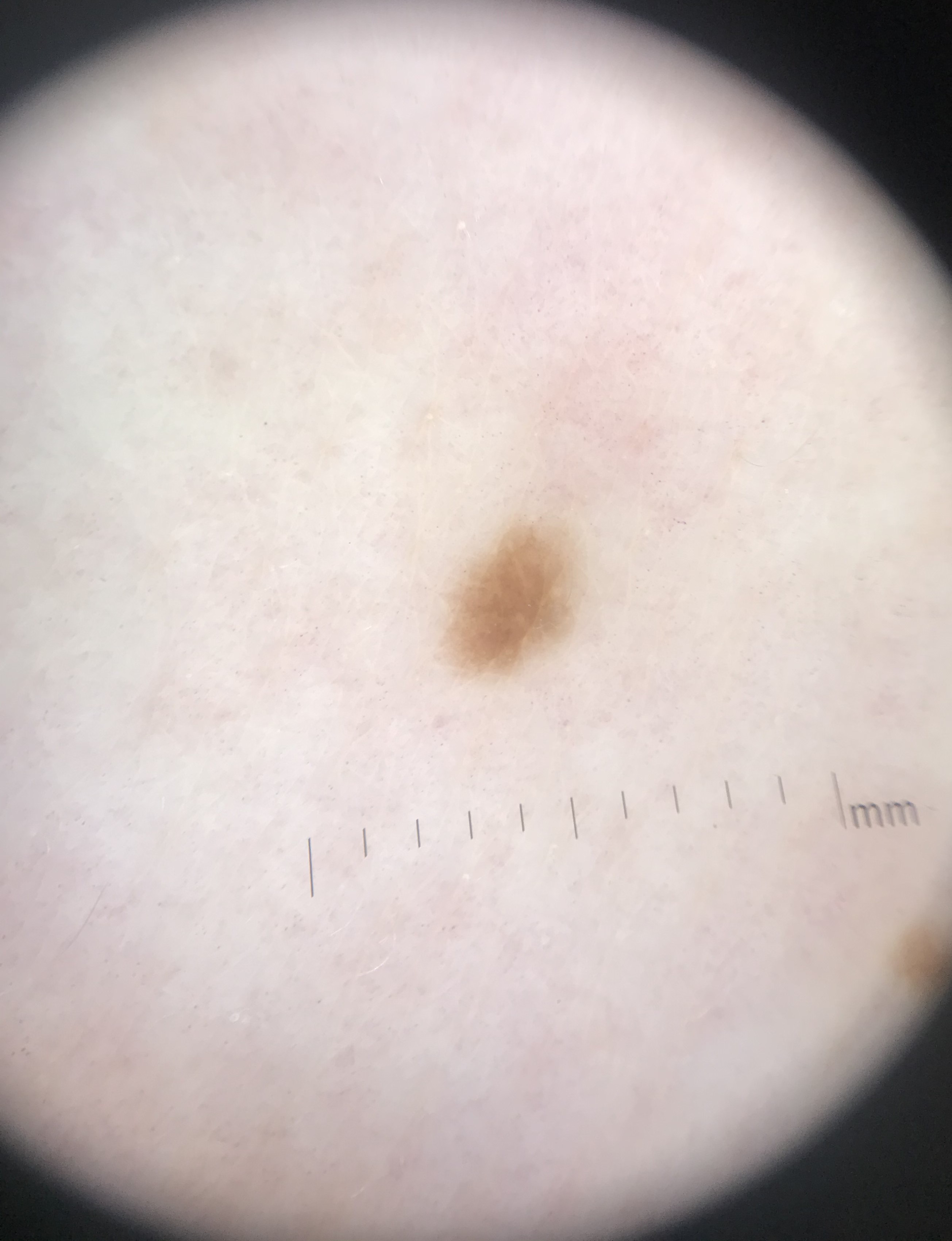Findings:
* image: dermoscopy
* subtype: keratinocytic
* class: seborrheic keratosis (expert consensus)